Located on the arm · an image taken at an angle · the patient is 18–29, male:
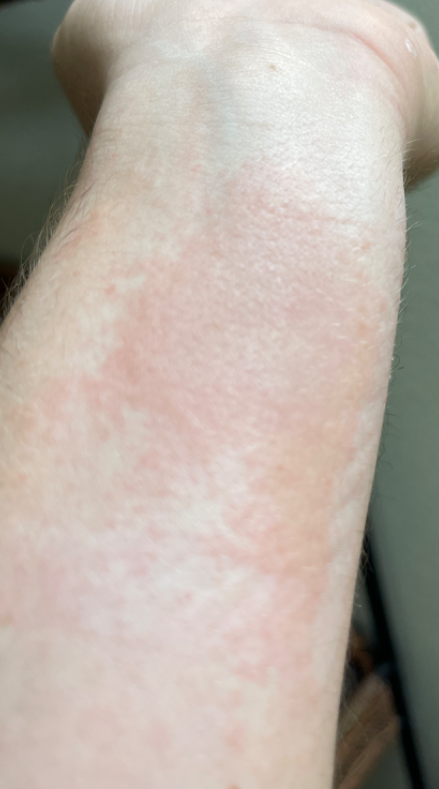Assessment: The reviewing clinician's impression was: the leading consideration is Allergic Contact Dermatitis; an alternative is Tinea; the differential also includes Eczema.